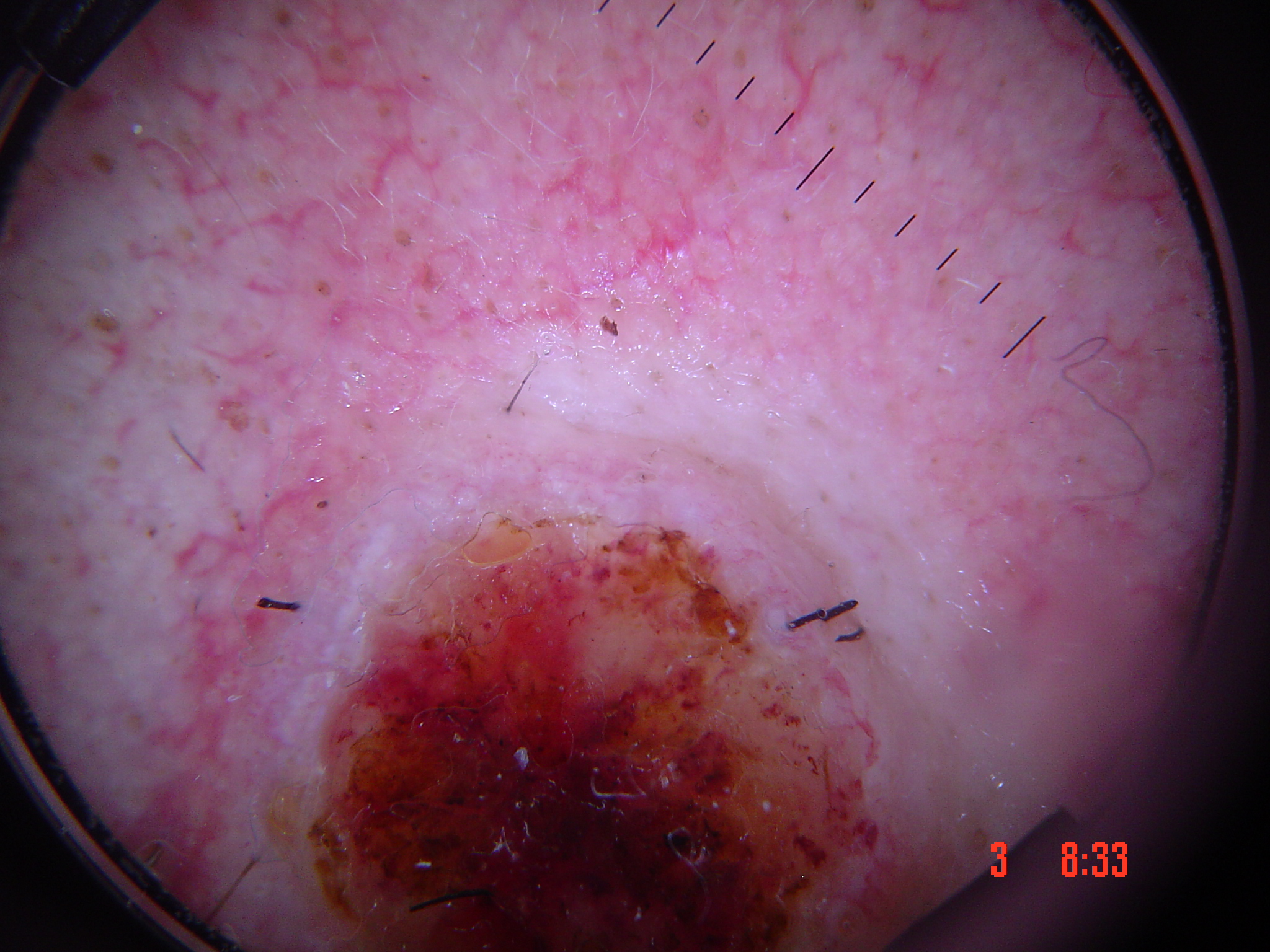Case:
A dermoscopic close-up of a skin lesion. The morphology is that of a keratinocytic lesion.
Conclusion:
Confirmed on histopathology as a squamous cell carcinoma.